A dermoscopic photograph of a skin lesion.
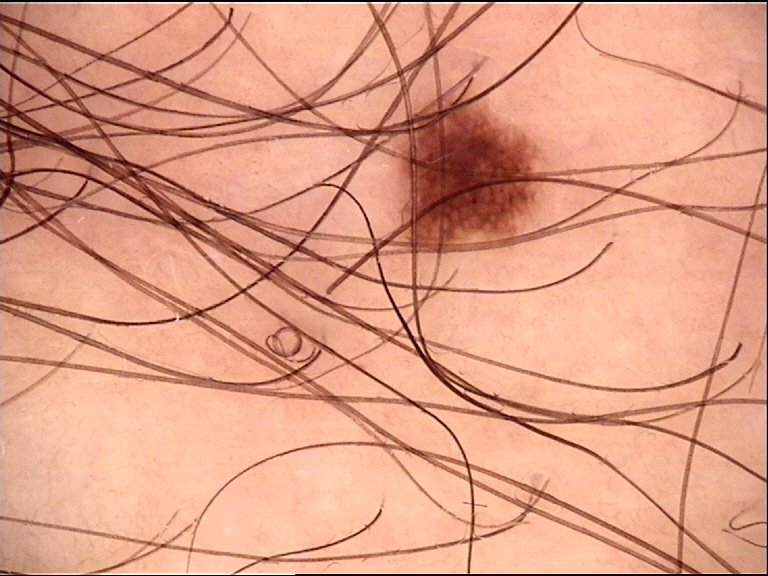Conclusion:
The diagnostic label was a dysplastic junctional nevus.